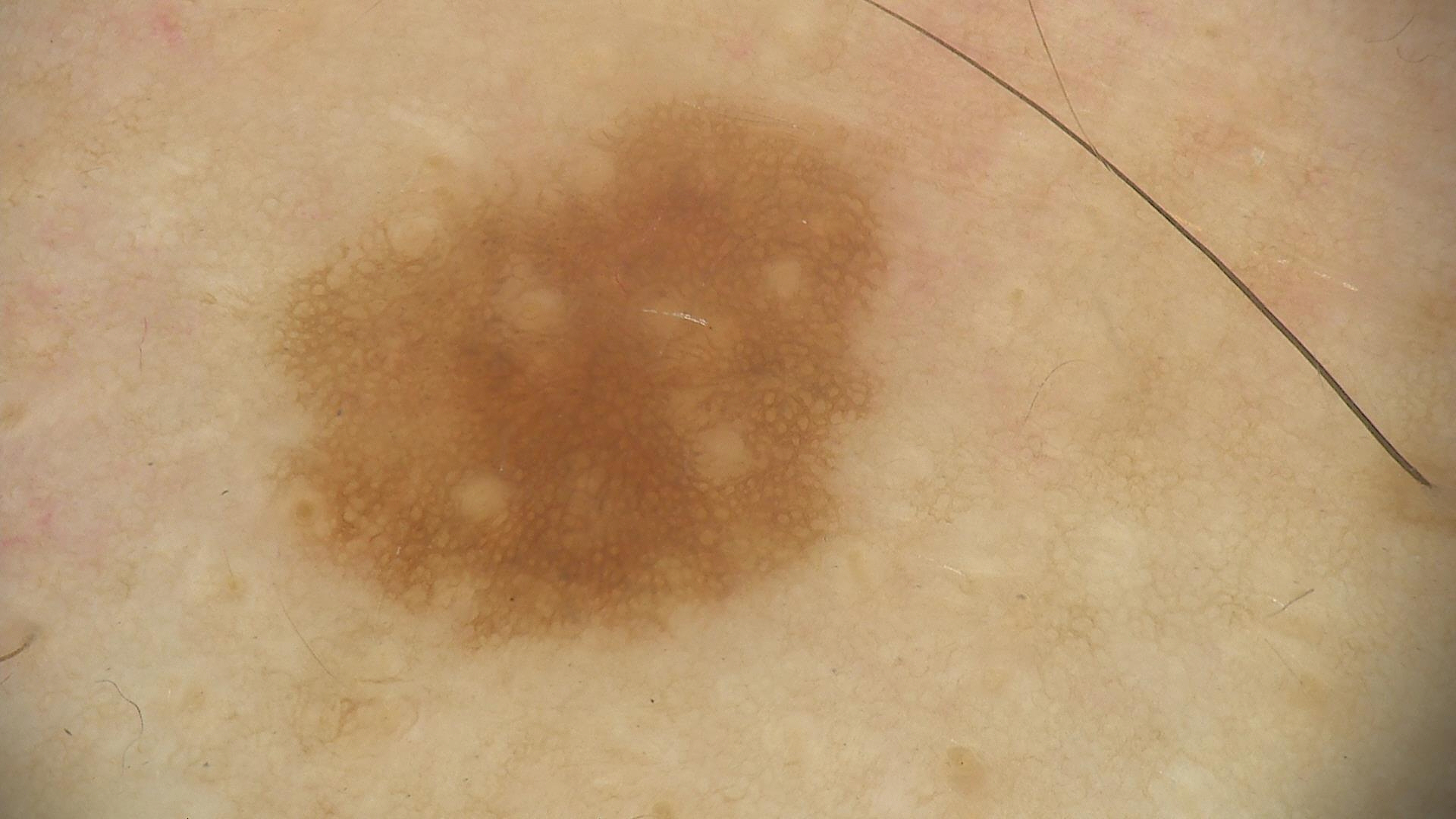class=junctional nevus (expert consensus).